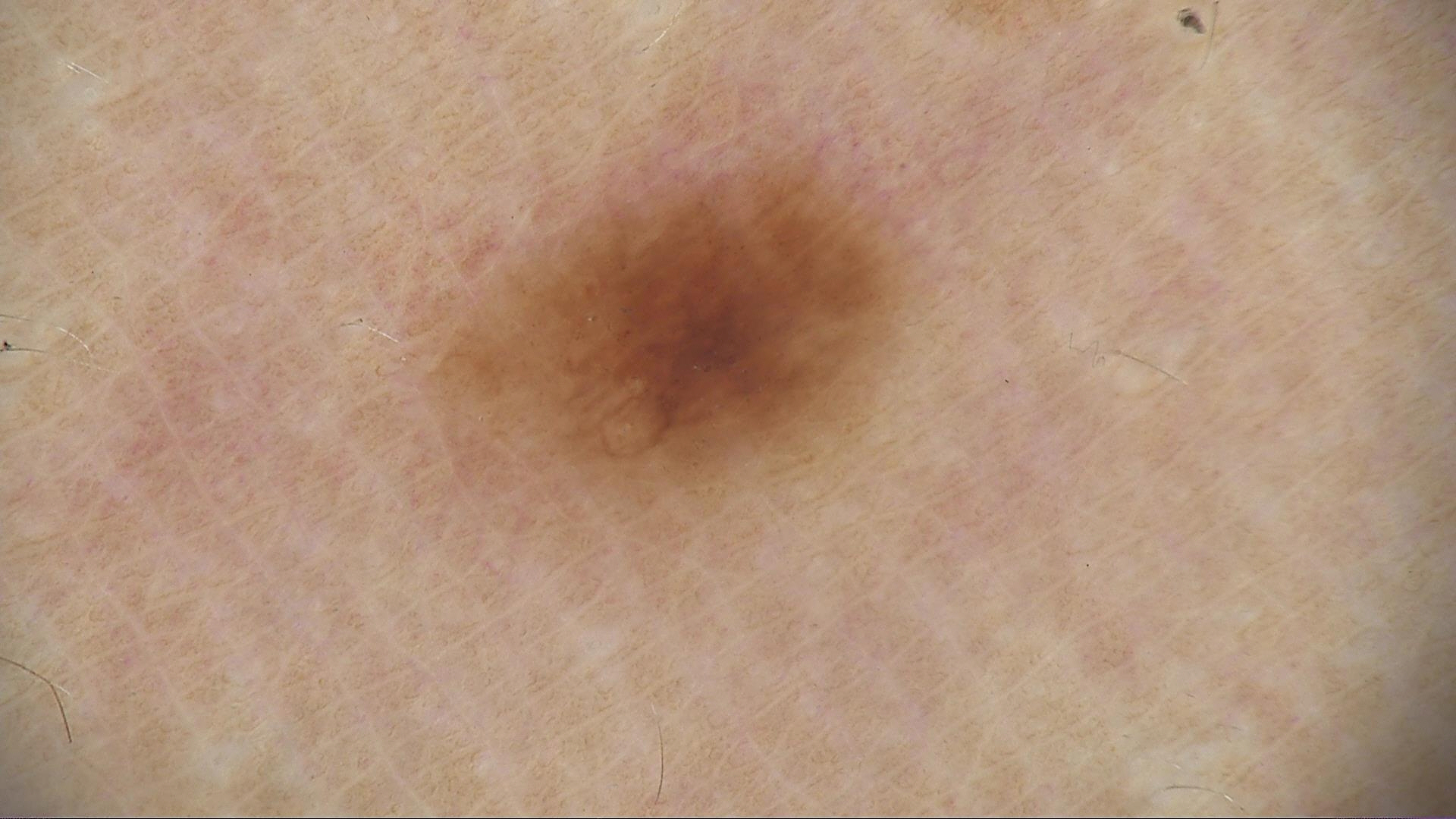Case: A dermoscopic photograph of a skin lesion. Conclusion: Labeled as a benign lesion — a dysplastic junctional nevus.